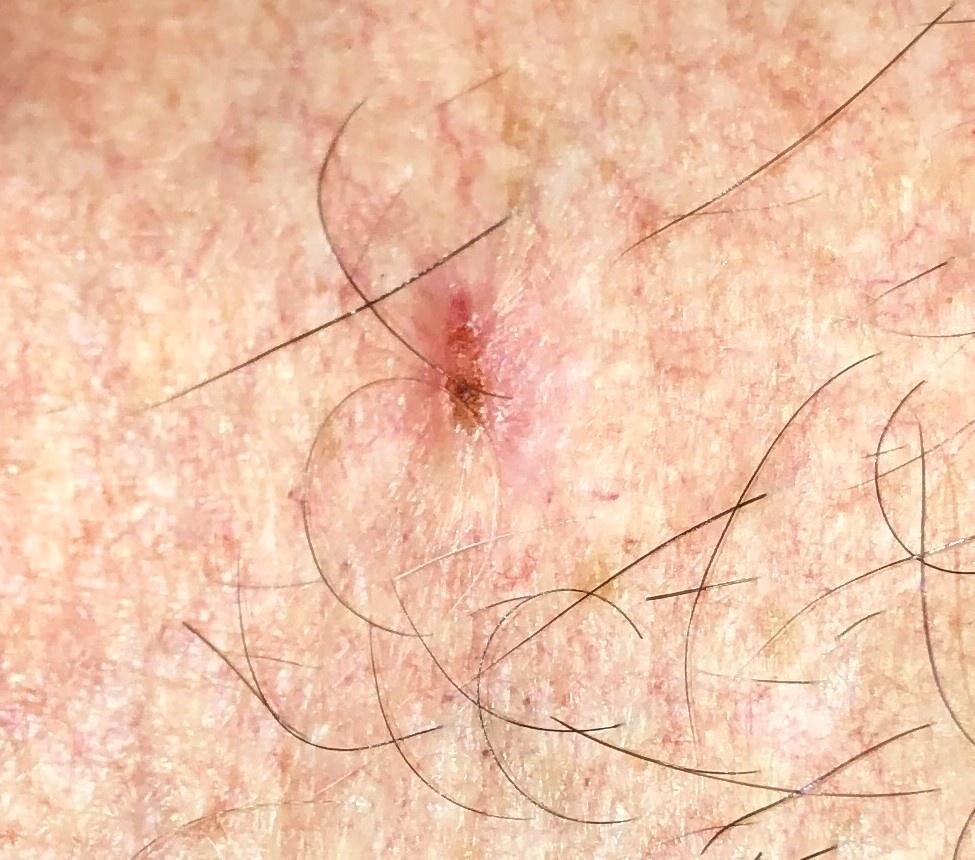subject: male, aged 58-62 | body site: the trunk | pathology: Basal cell carcinoma (biopsy-proven).